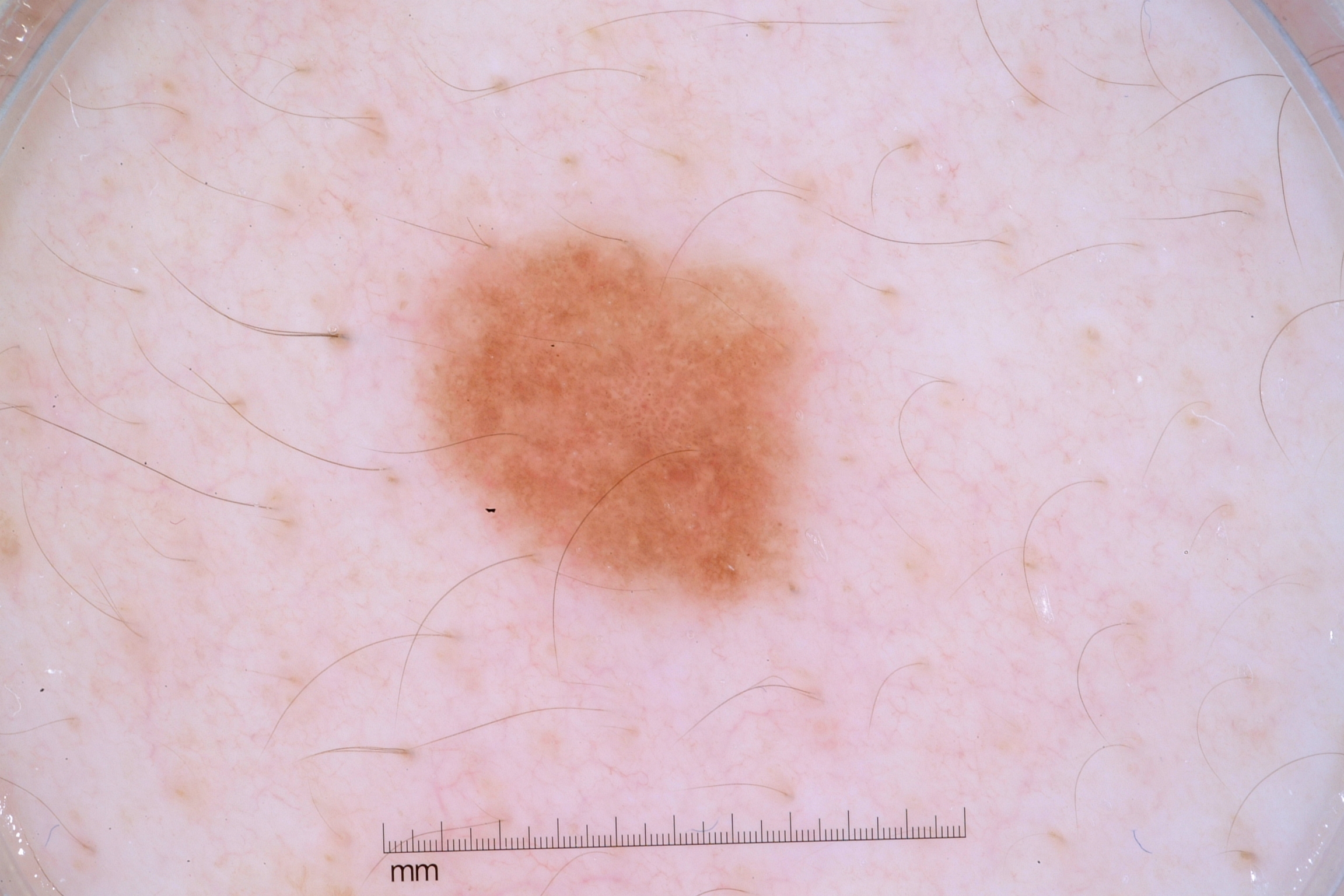Findings:
– imaging · dermoscopic image
– patient · male, aged approximately 40
– extent · ~10% of the field
– features · pigment network, milia-like cysts, and negative network
– lesion location · x1=420 y1=232 x2=818 y2=609
– assessment · a melanocytic nevus